This is a close-up image · Fitzpatrick IV:
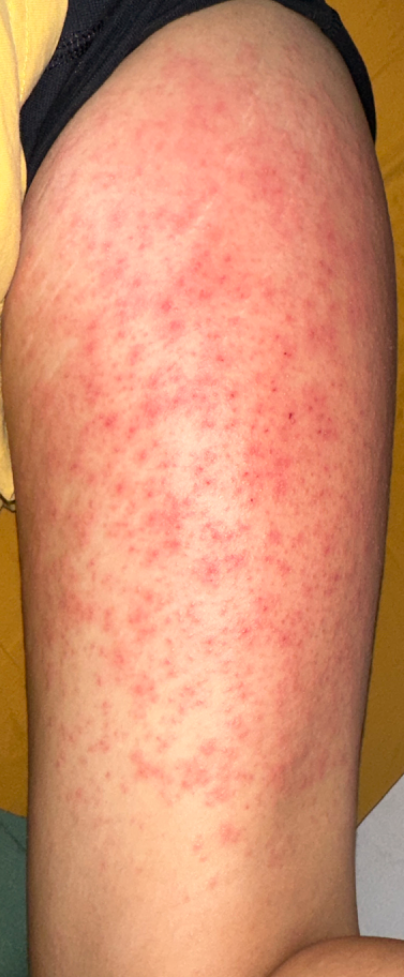Findings: The differential, in no particular order, includes Eczema and Allergic Contact Dermatitis.